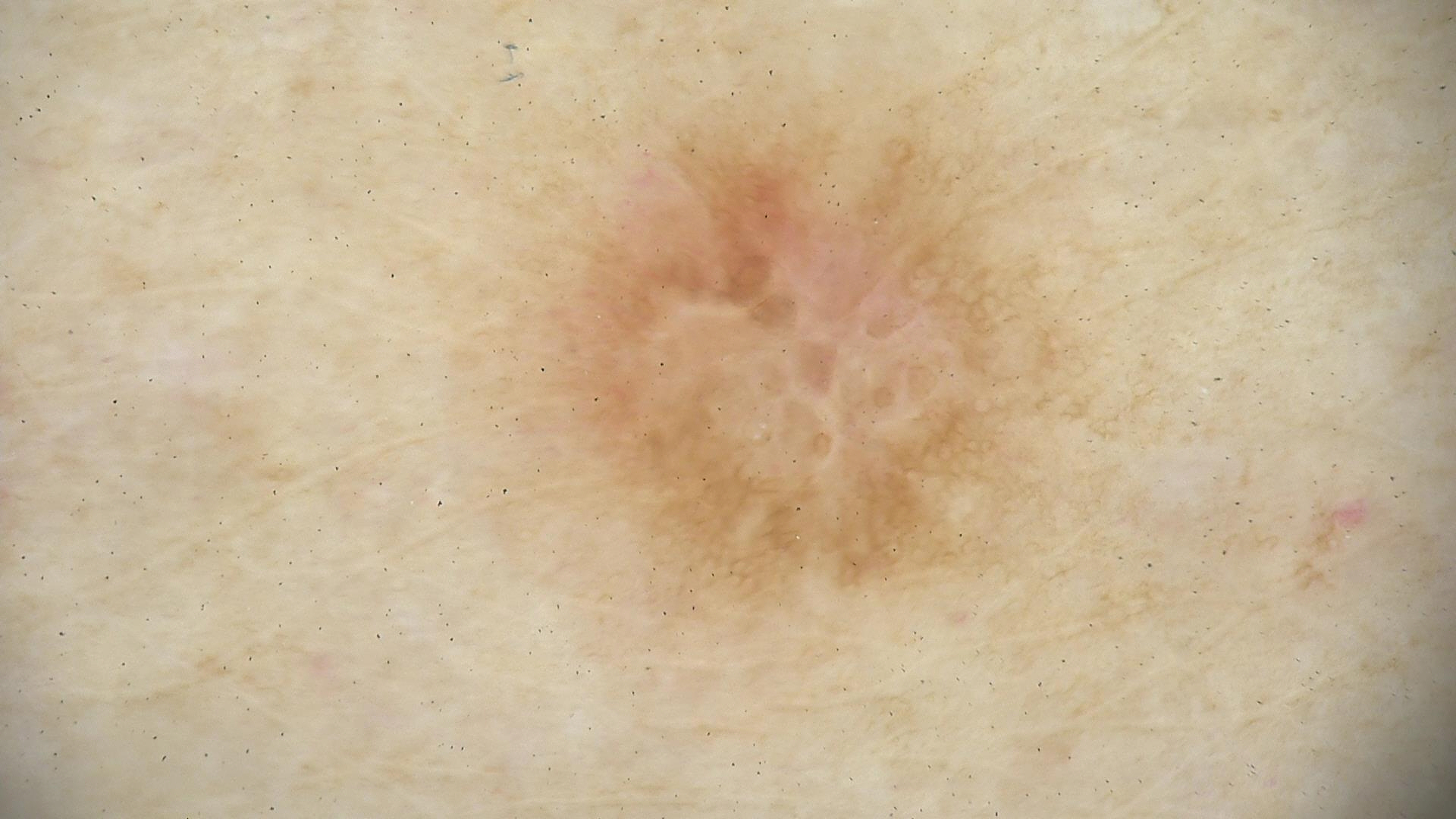Findings: A dermoscopy image of a single skin lesion. This is a fibro-histiocytic lesion. Conclusion: Consistent with a benign lesion — a dermatofibroma.